A skin lesion imaged with a dermatoscope: 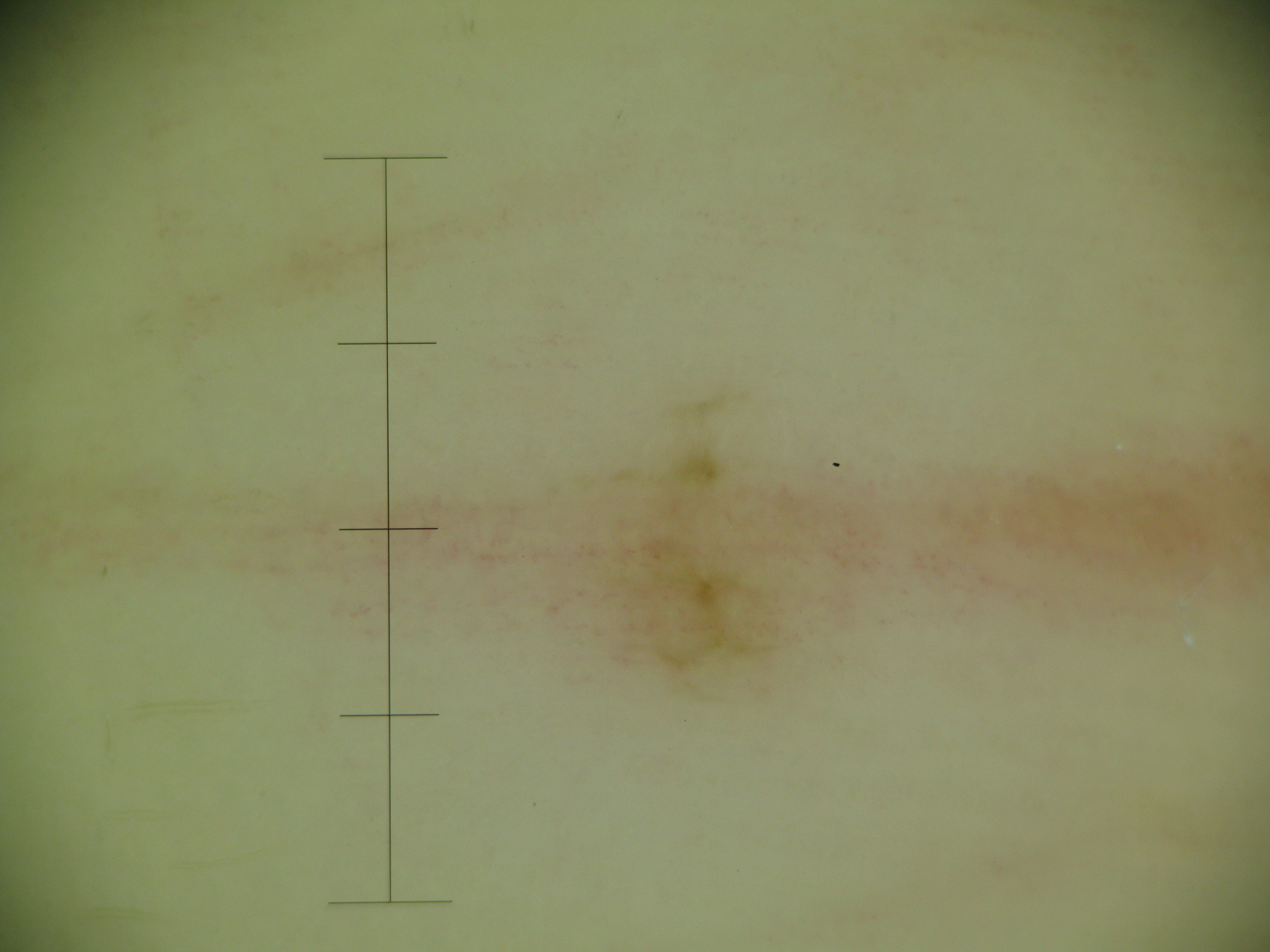diagnosis — acral junctional nevus (expert consensus).